A skin lesion imaged with a dermatoscope.
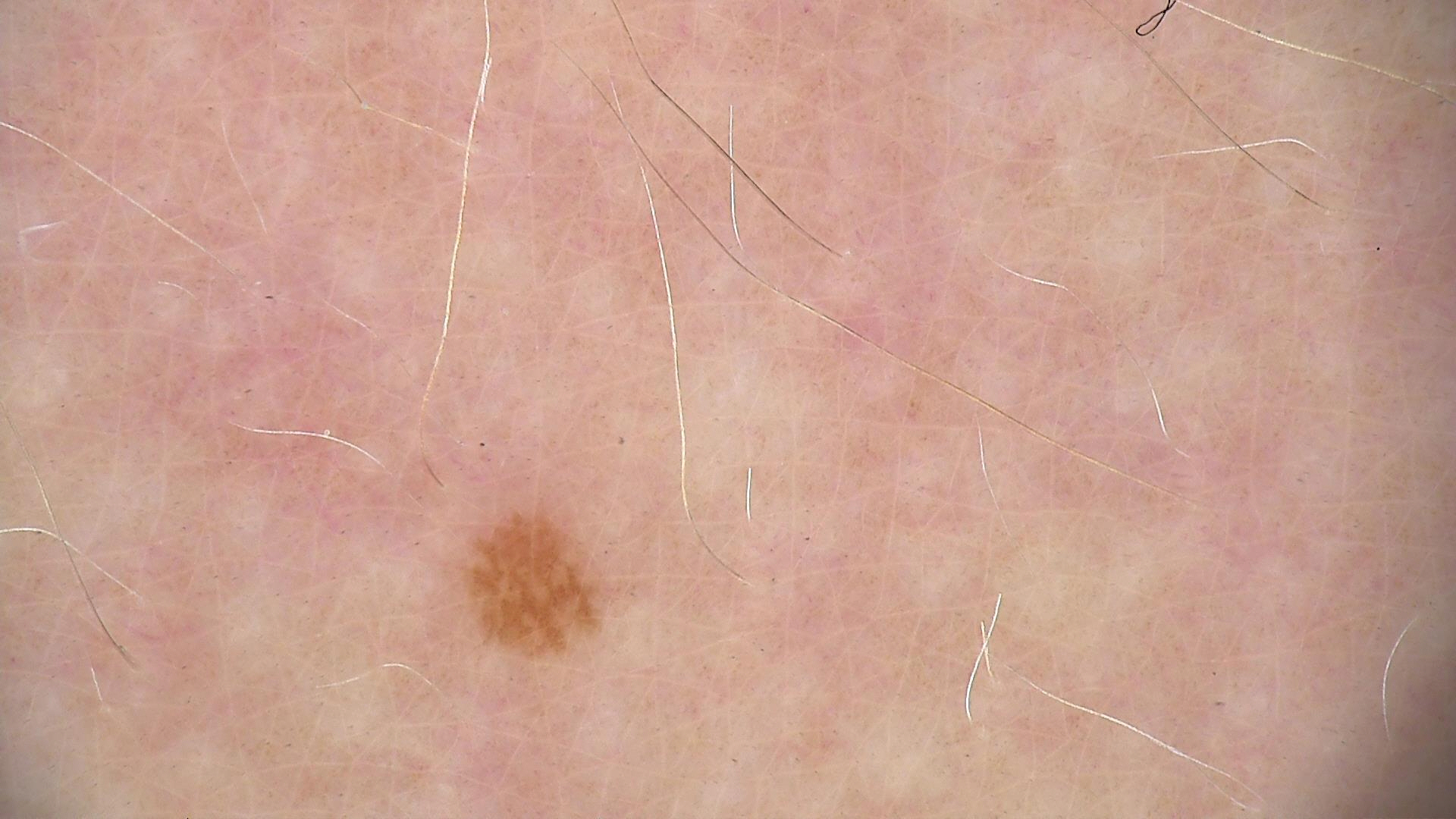Conclusion:
The diagnosis was a dysplastic junctional nevus.